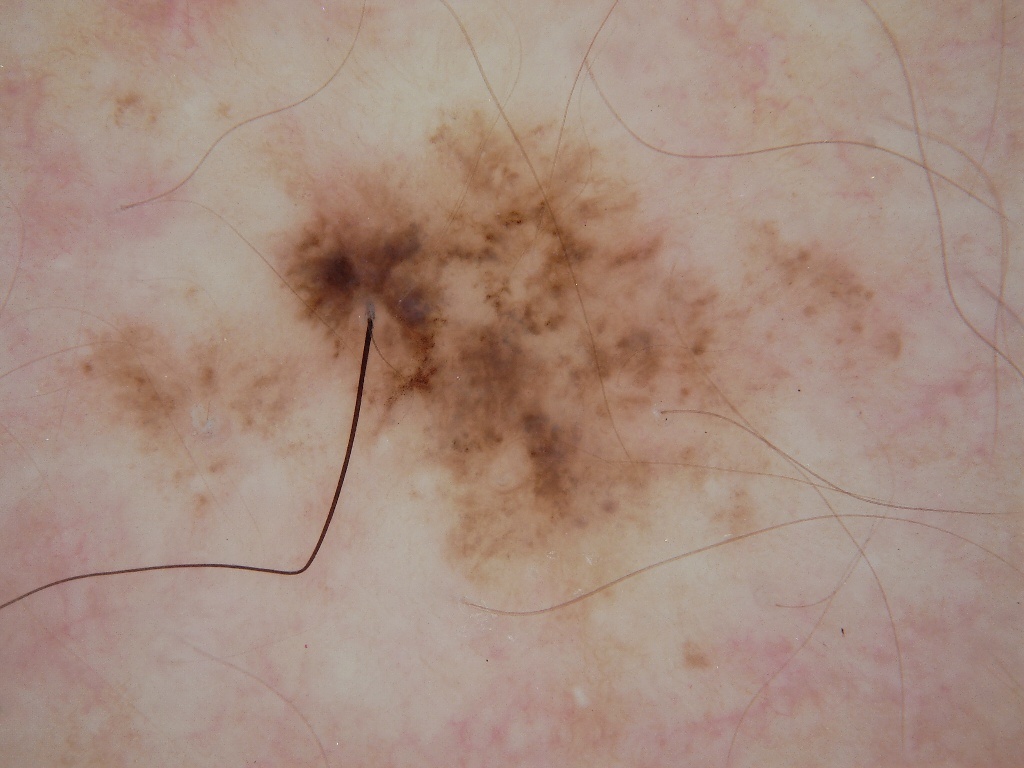| key | value |
|---|---|
| subject | female, in their mid- to late 20s |
| image | dermoscopic image |
| dermoscopic findings | globules; absent: pigment network, negative network, milia-like cysts, and streaks |
| location | <bbox>68, 81, 913, 601</bbox> |
| diagnosis | a melanocytic nevus, a benign skin lesion |